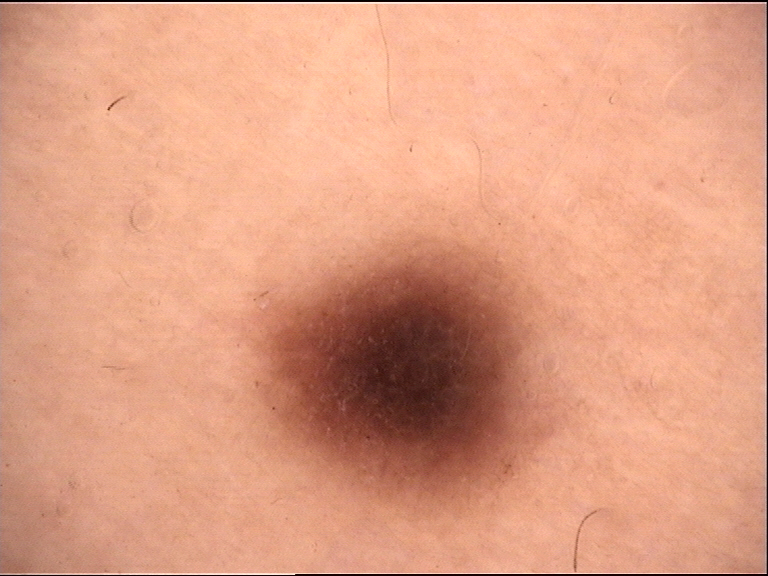Conclusion:
Consistent with a junctional nevus.